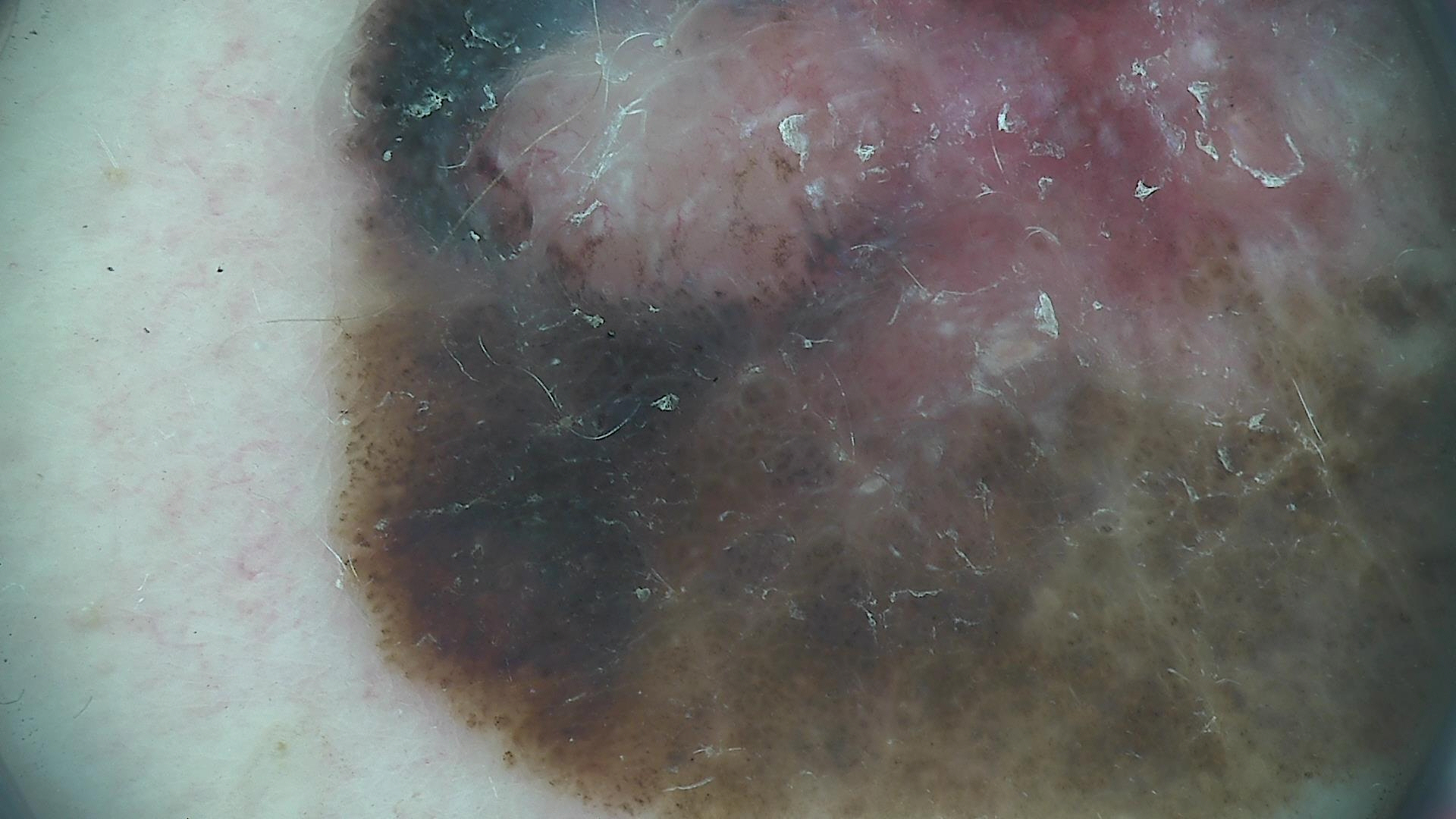Conclusion: Histopathology confirmed a melanoma.